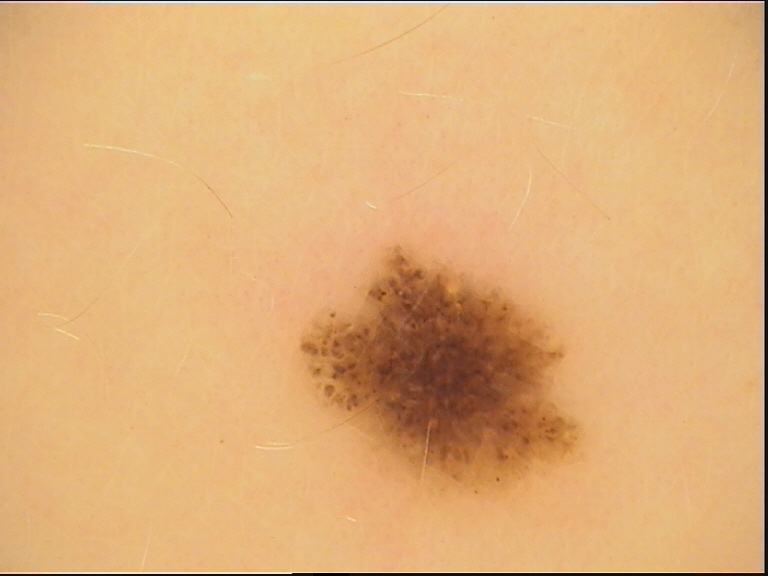The diagnosis was a dysplastic junctional nevus.